The subject is 30–39, female; the photograph is a close-up of the affected area.
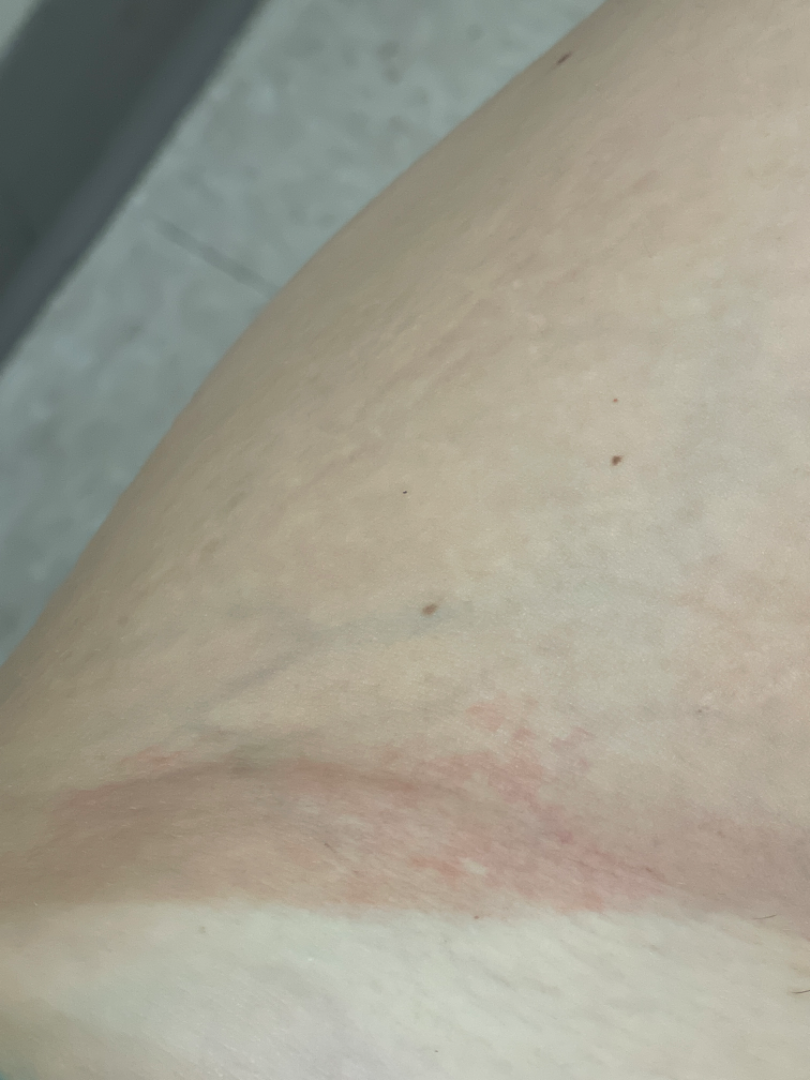The contributor notes itching.
FST III; human graders estimated MST 3 (US pool) or 2 (India pool).
The patient described the issue as a rash.
Texture is reported as raised or bumpy.
Intertrigo and Allergic Contact Dermatitis were each considered, in no particular order; an alternative is Irritant Contact Dermatitis.